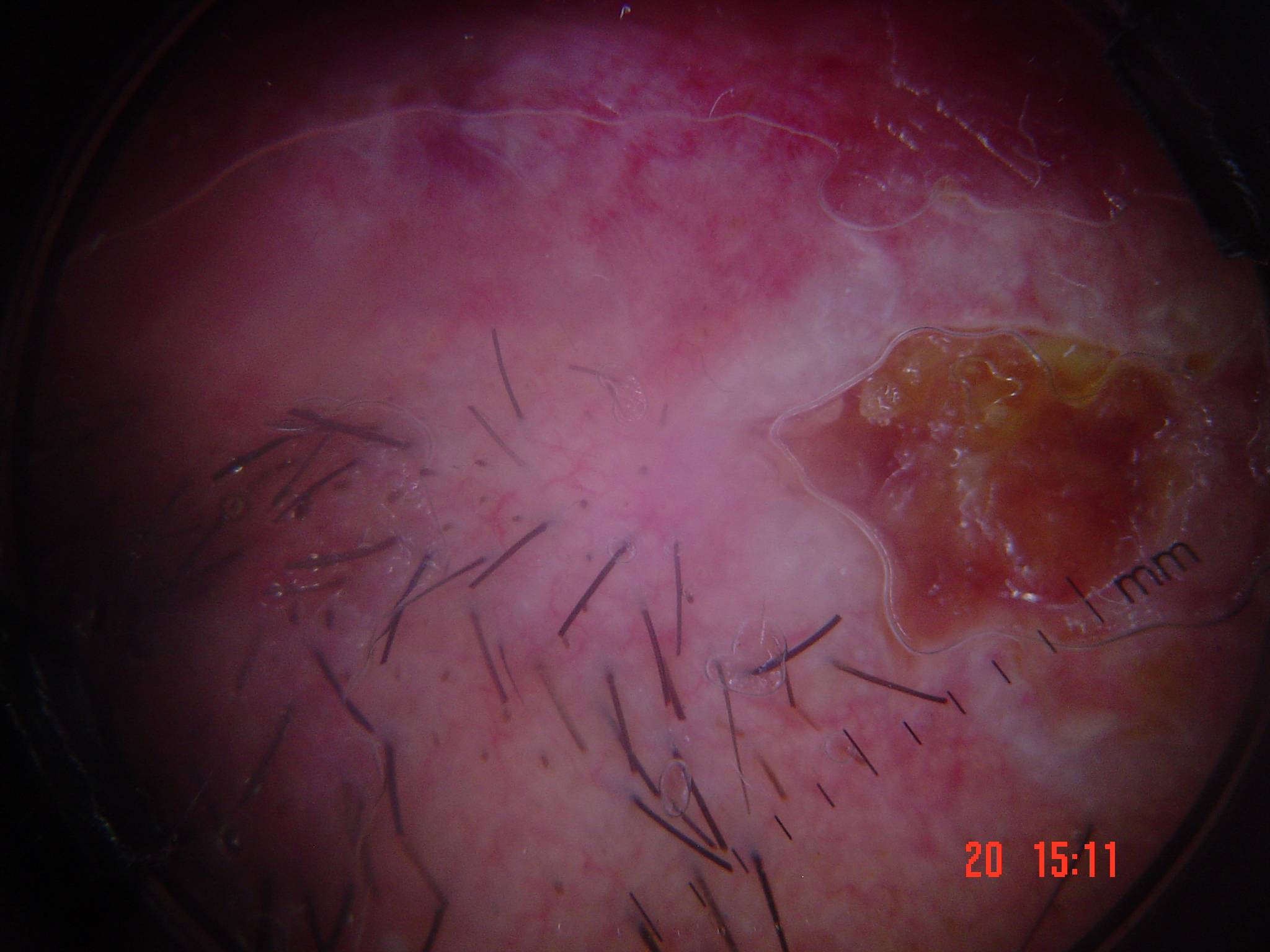The architecture is that of a keratinocytic lesion.
Biopsy-confirmed as a skin cancer — a squamous cell carcinoma.